A dermoscopic close-up of a skin lesion: 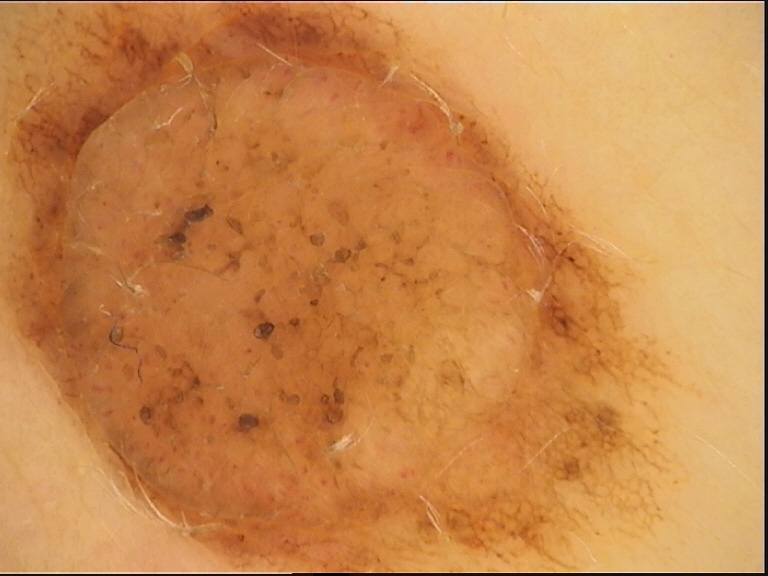The diagnosis was a dermal nevus.